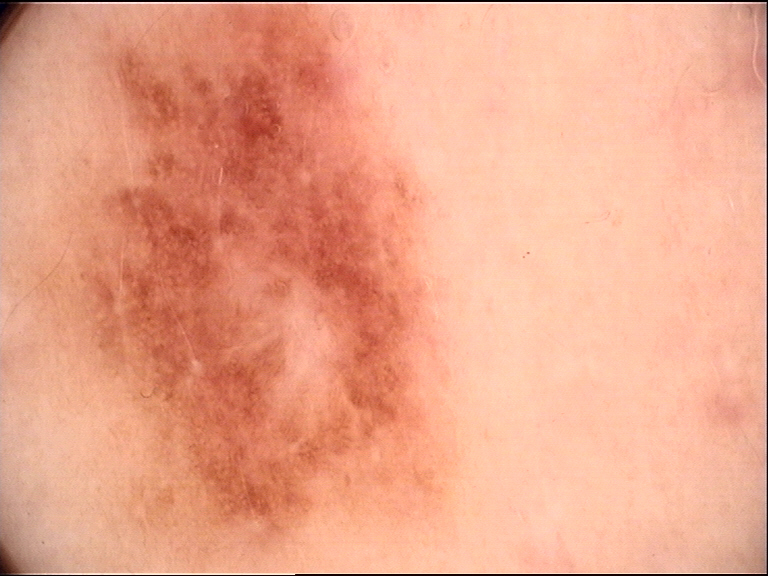Dermoscopy of a skin lesion. Classified as a dysplastic junctional nevus.